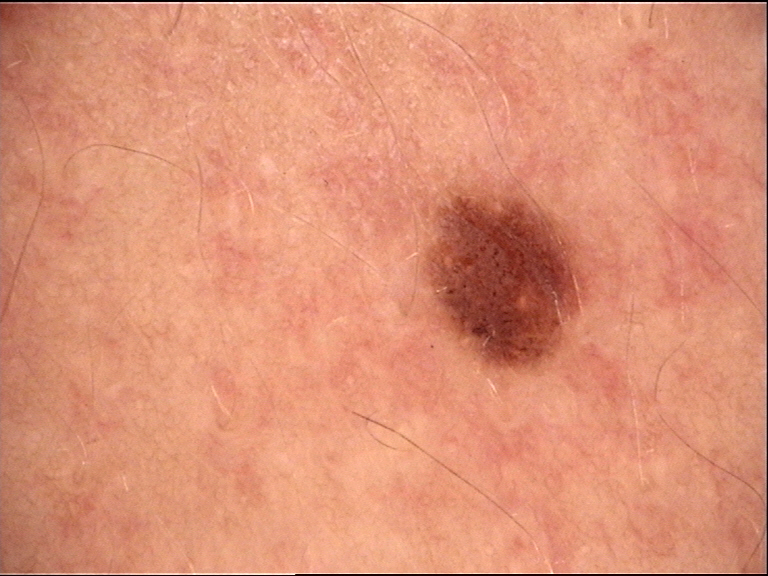class = dysplastic junctional nevus (expert consensus).